This image was taken at a distance; the affected area is the back of the torso:
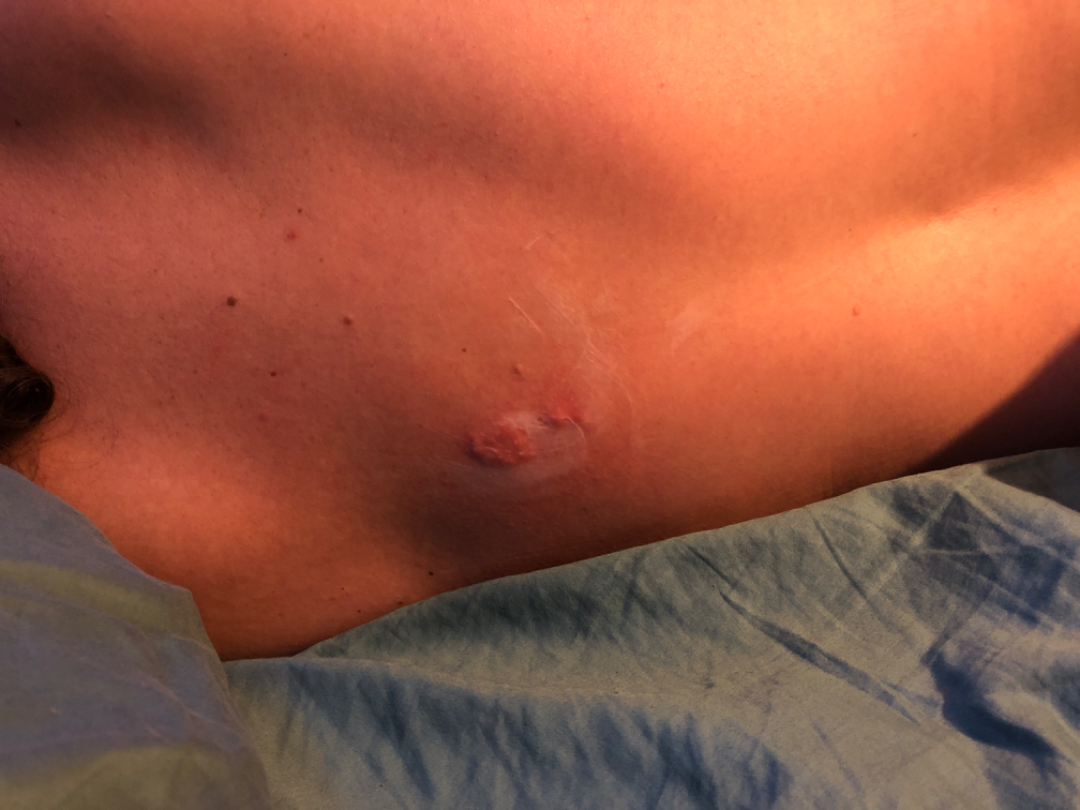differential diagnosis: Folliculitis (0.62); Herpes Simplex (0.26); Deep fungal infection (0.12).